The photograph is a close-up of the affected area; the back of the hand and arm are involved.
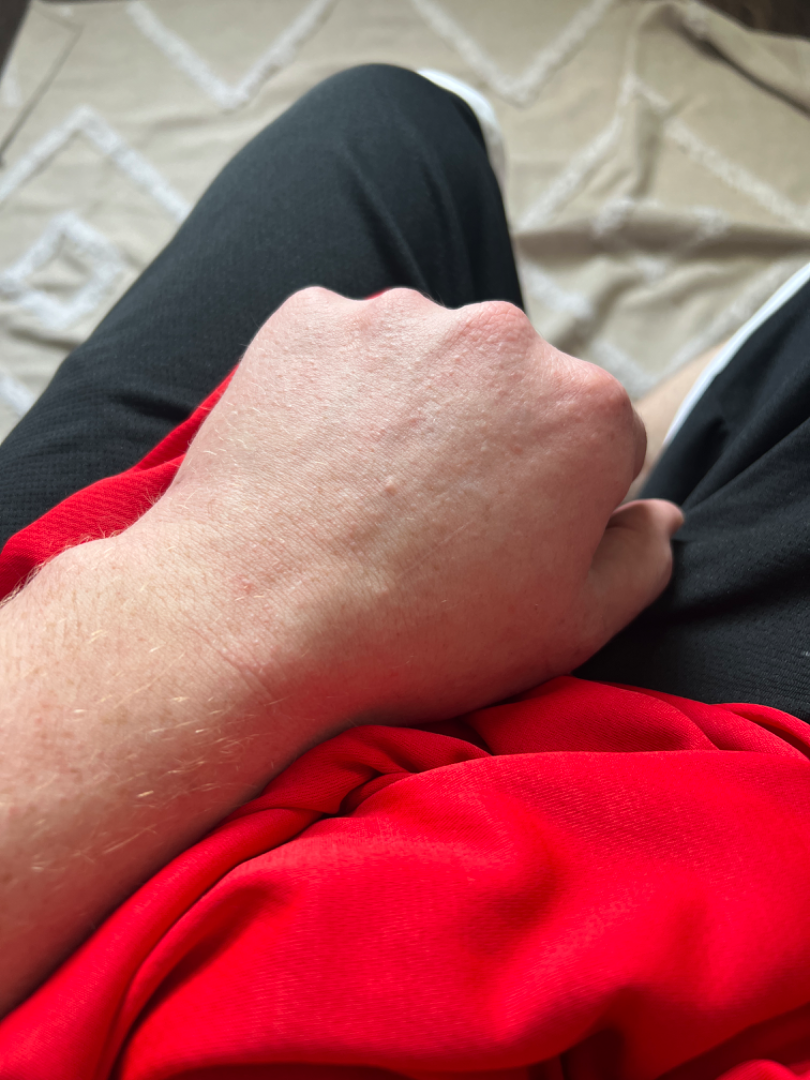assessment = indeterminate